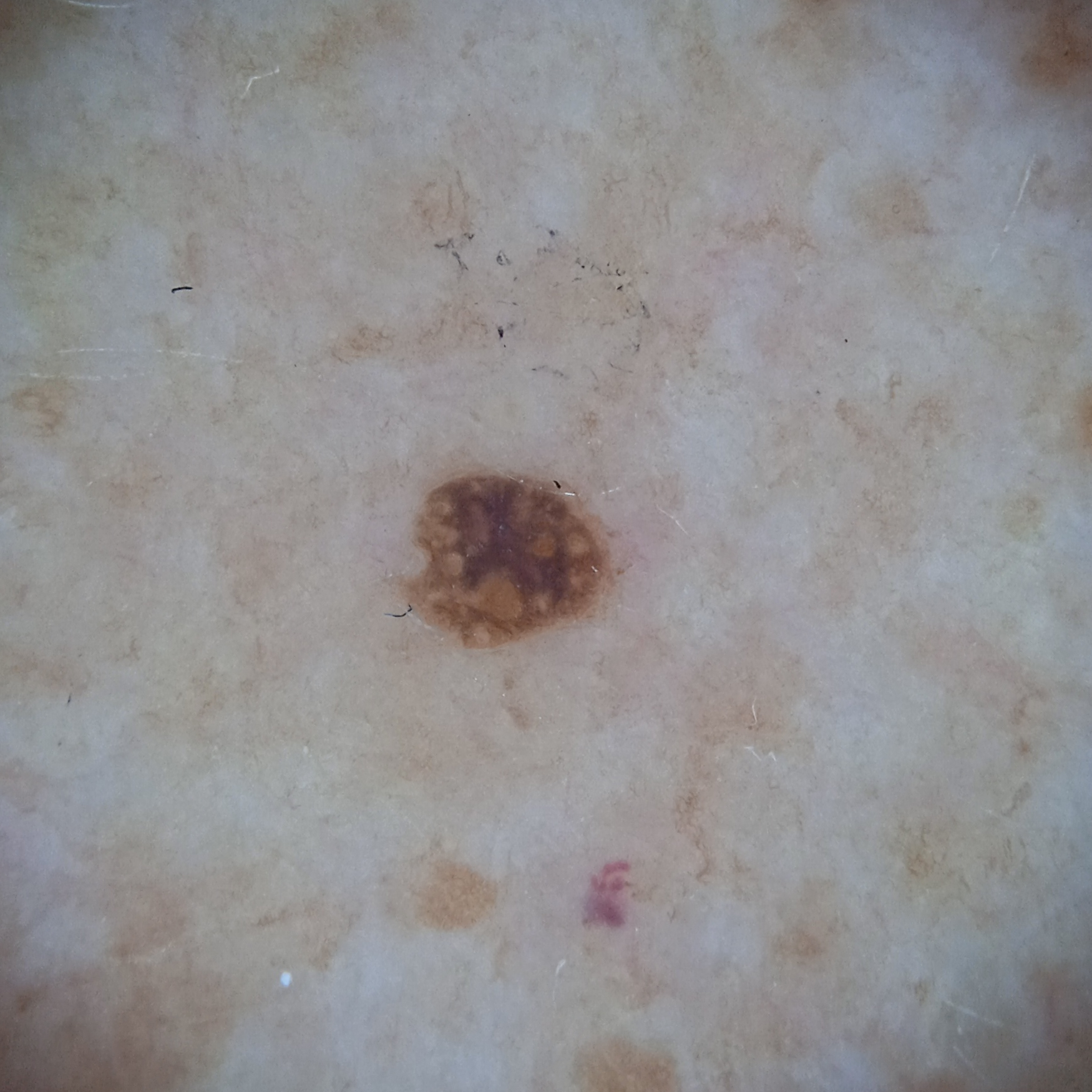nevus count: numerous melanocytic nevi; sun reaction: skin tans without first burning; clinical context: research study (no referral diagnosis); patient: female, 78 years old; image: dermatoscopic image; diameter: 2.4 mm; diagnosis: seborrheic keratosis (dermatologist consensus).